A male subject 66 years old · the patient describes having few moles overall · a skin lesion imaged with a dermatoscope · on a questionnaire the patient reported a prior organ transplant.
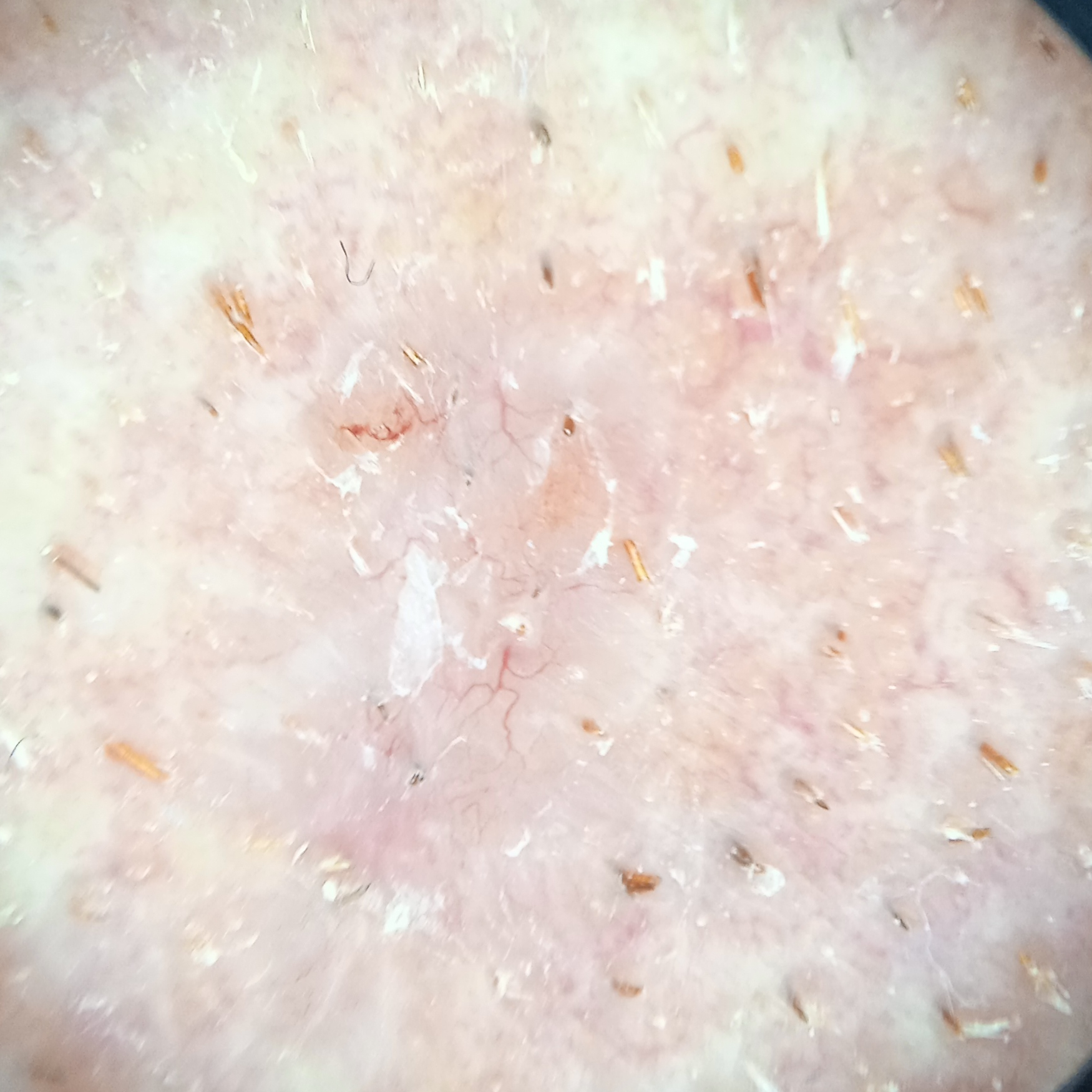The lesion is located on the face. The lesion measures approximately 7.5 mm. Histopathologically confirmed as a basal cell carcinoma, following excision, with a measured tumor thickness of 1.9 mm.